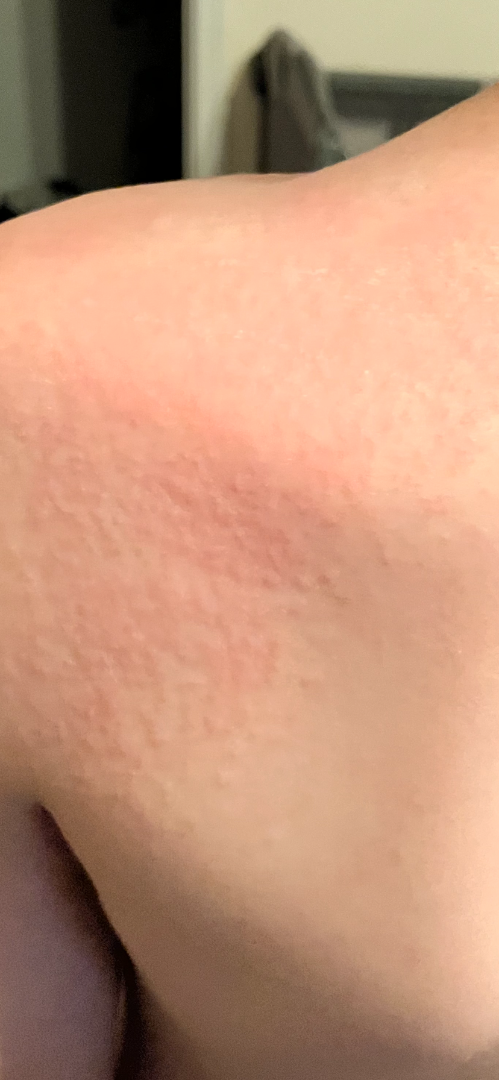Notes:
• assessment · ungradable on photographic review
• framing · close-up
• skin tone · Fitzpatrick phototype III; lay graders estimated Monk Skin Tone 2–3
• lesion texture · raised or bumpy
• duration · about one day
• site · back of the torso and arm